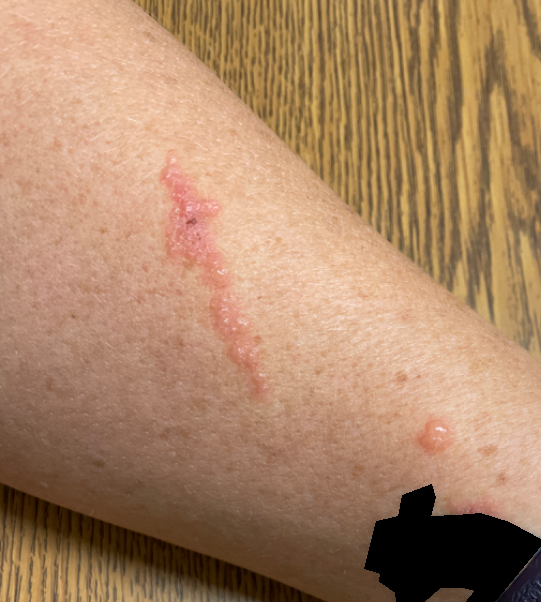The skin condition could not be confidently assessed from this image. No constitutional symptoms were reported. The affected area is the arm. This image was taken at a distance. Texture is reported as raised or bumpy. Female contributor, age 50–59.